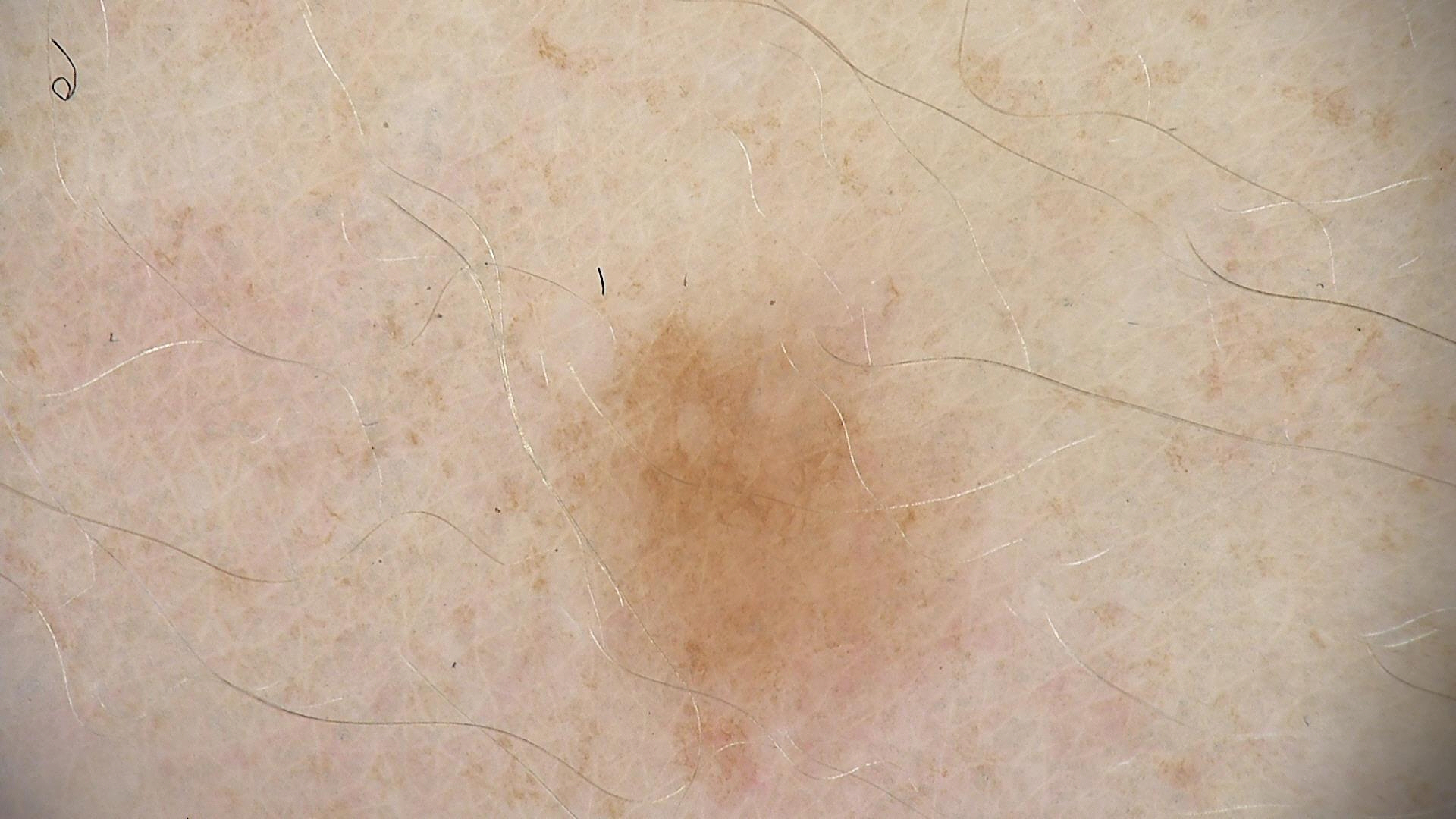A dermoscopic photograph of a skin lesion. Classified as a dysplastic junctional nevus.